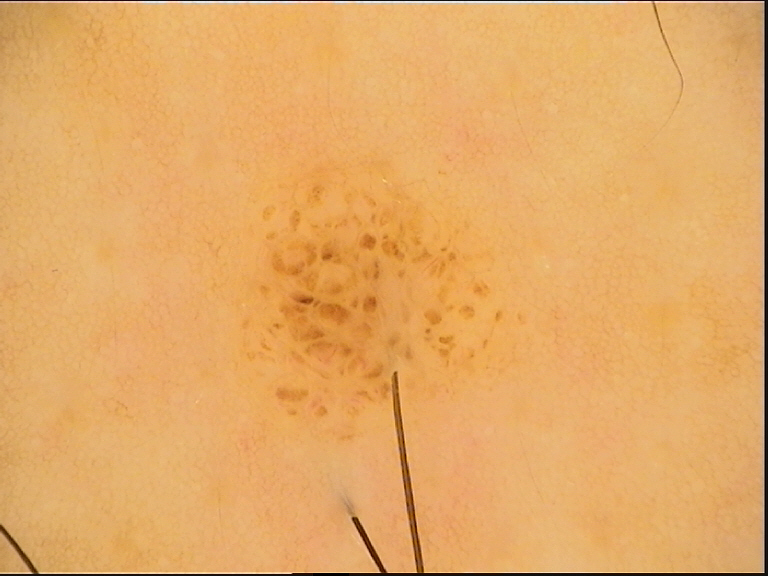imaging=dermoscopy; class=compound nevus (expert consensus).